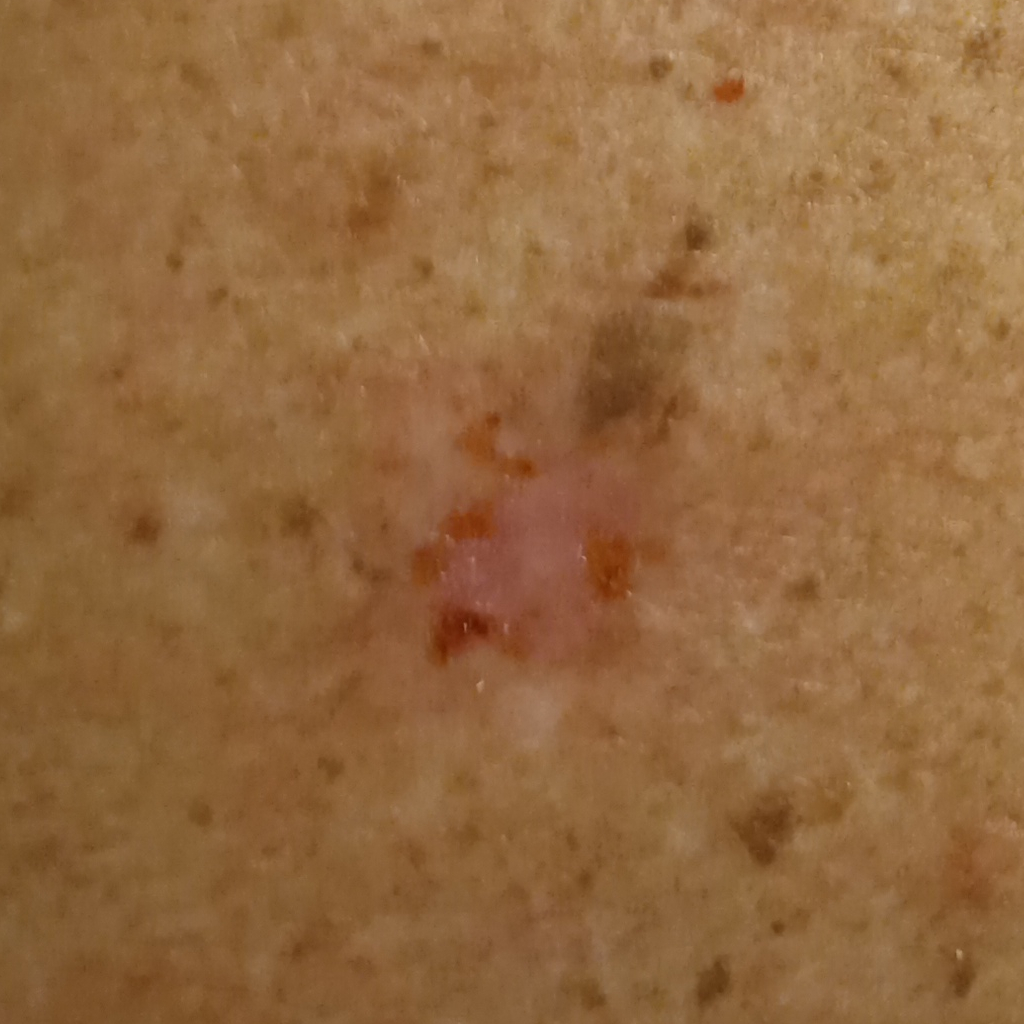Summary:
The patient says their skin reddens with sun exposure. The patient reports a personal history of cancer and a family history of skin cancer. The patient describes having few moles overall. The referring clinician suspected basal cell carcinoma. A clinical photograph showing a skin lesion. A male patient aged 81. Located on the back. The lesion is about 12.6 mm across.
Conclusion:
Histopathologically confirmed as a basal cell carcinoma, following excision, with a measured thickness of 3 mm.